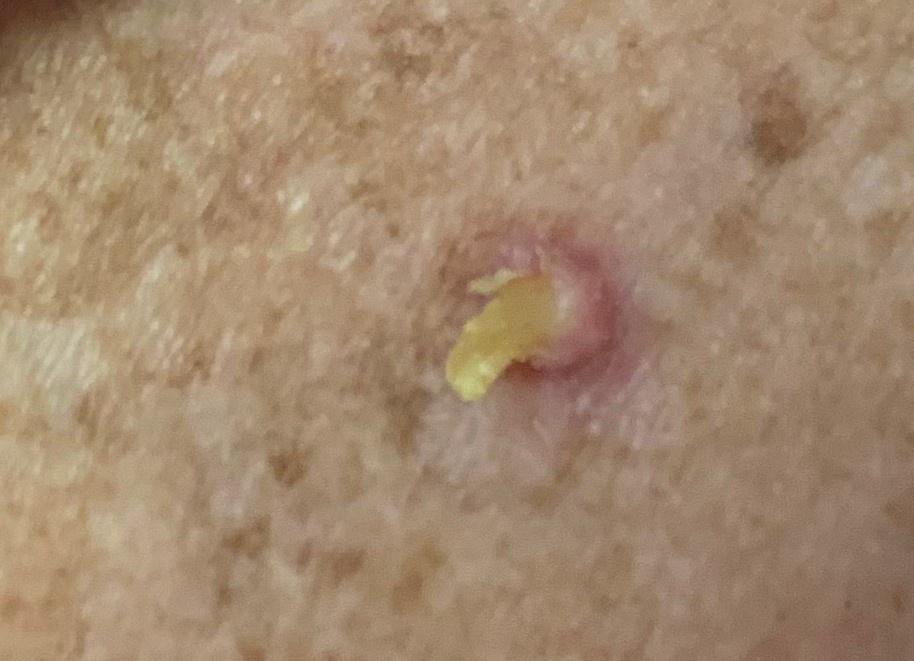Q: What did the workup show?
A: Squamous cell carcinoma (biopsy-proven)